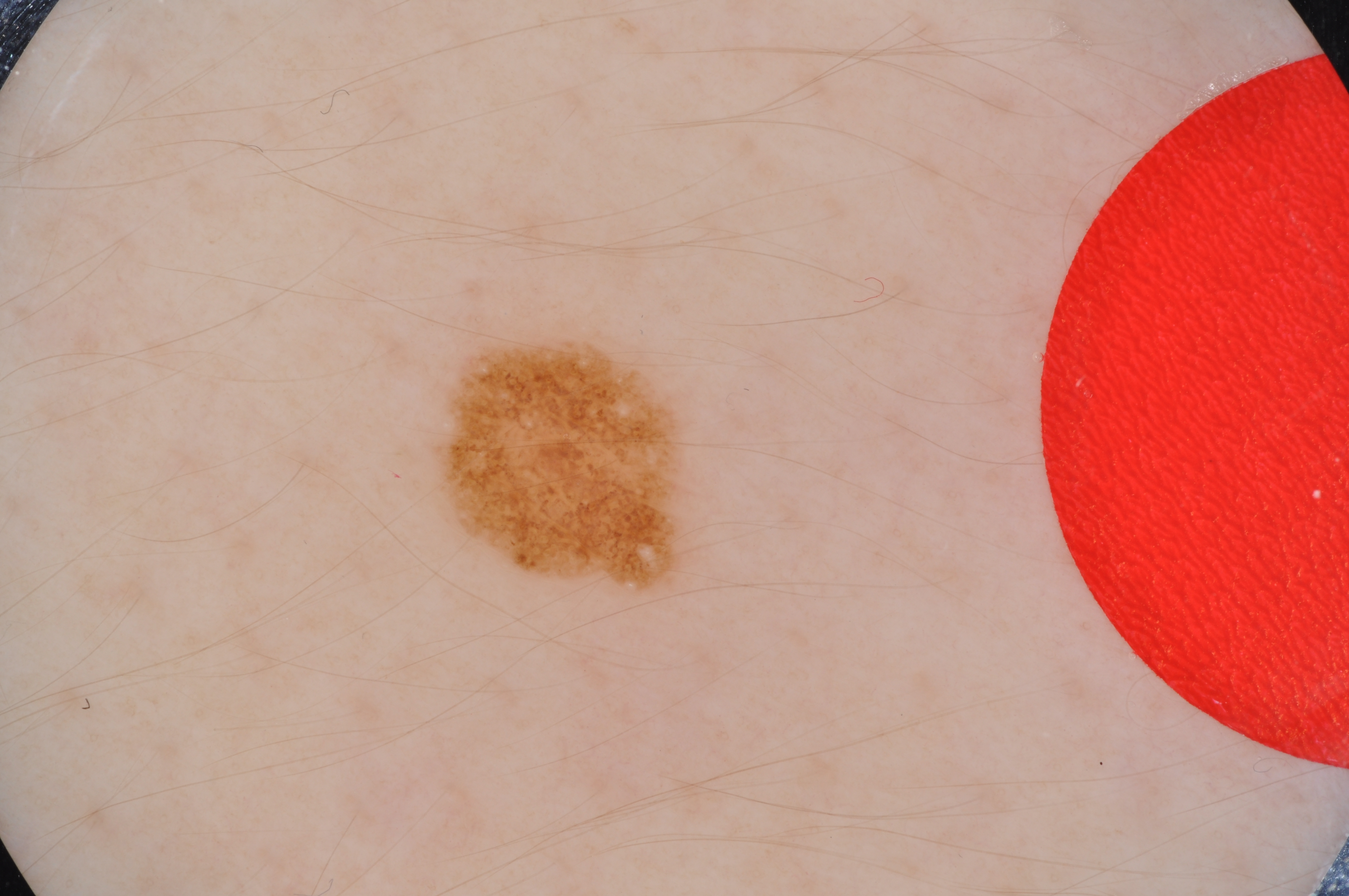Findings: The patient is a male about 15 years old. A skin lesion imaged with a dermatoscope. As (left, top, right, bottom), the lesion occupies the region 434 341 681 593. Dermoscopy demonstrates milia-like cysts and globules; no negative network, streaks, or pigment network. Impression: The diagnostic assessment was a melanocytic nevus.